A dermoscopic photograph of a skin lesion.
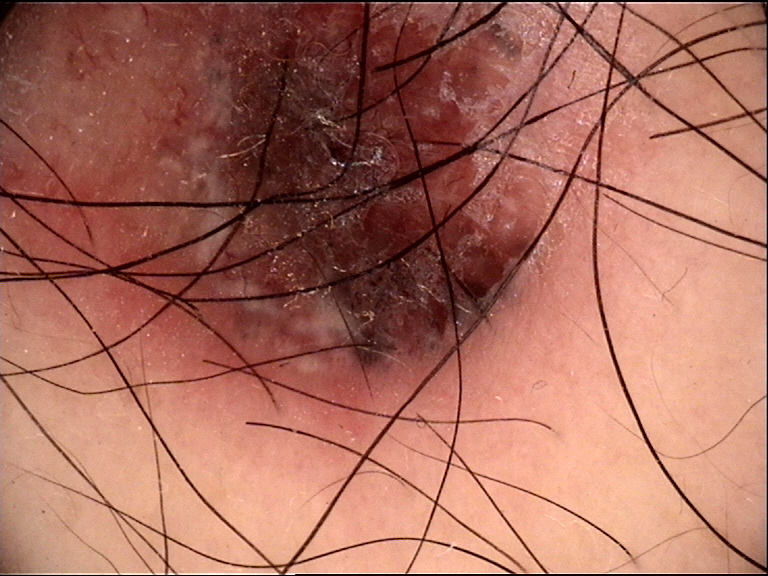classification: keratinocytic
class: basal cell carcinoma (biopsy-proven)